A subject age 55. A clinical photograph of a skin lesion.
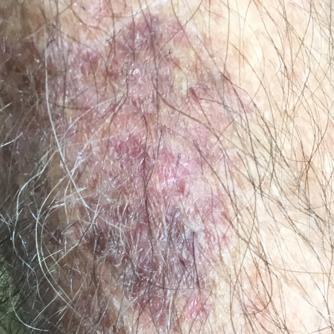Q: What is the anatomic site?
A: a forearm
Q: What was the clinical impression?
A: actinic keratosis (clinical consensus)